This is a dermoscopic photograph of a skin lesion. A female subject aged 23 to 27.
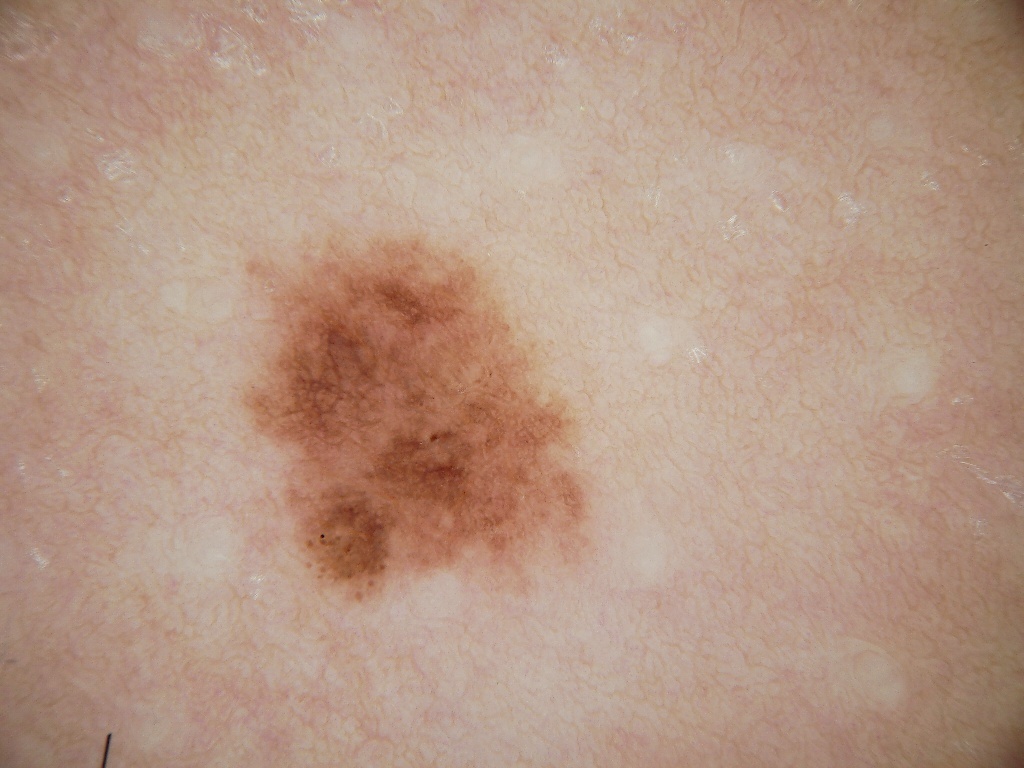dermoscopic findings = pigment network and globules; absent: negative network, milia-like cysts, and streaks
lesion bbox = x1=221 y1=220 x2=619 y2=616
extent = moderate
assessment = a melanocytic nevus